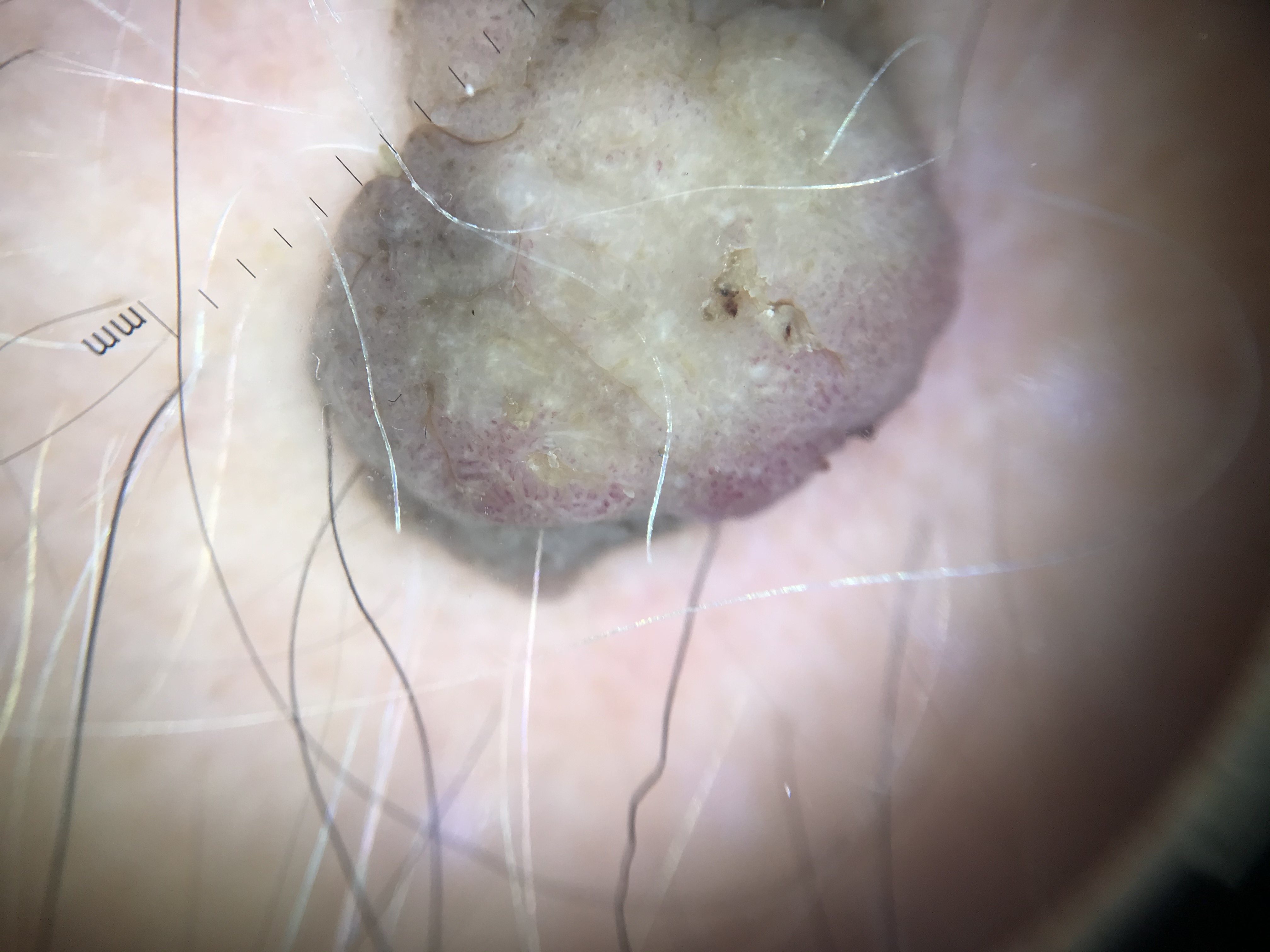- diagnosis — seborrheic keratosis (expert consensus)